The lesion involves the front of the torso, back of the torso and head or neck. The patient considered this skin that appeared healthy to them. Skin tone: Fitzpatrick III. The lesion is described as rough or flaky. Symptoms reported: itching. Male subject, age 18–29. A close-up photograph:
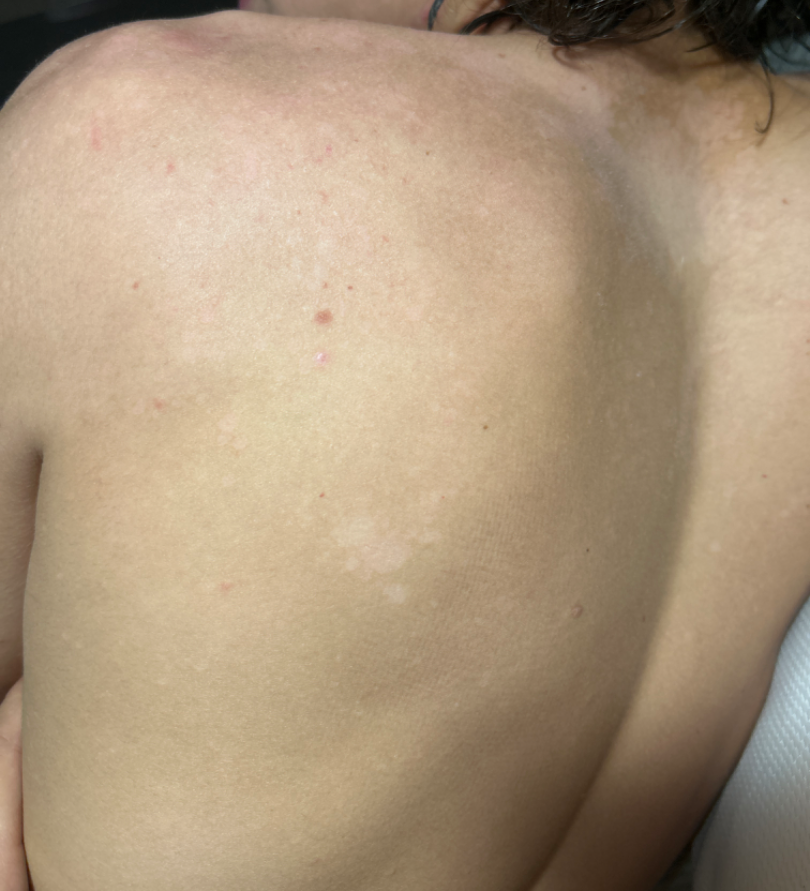assessment = the impression on review was Tinea Versicolor.